This is a dermoscopic photograph of a skin lesion.
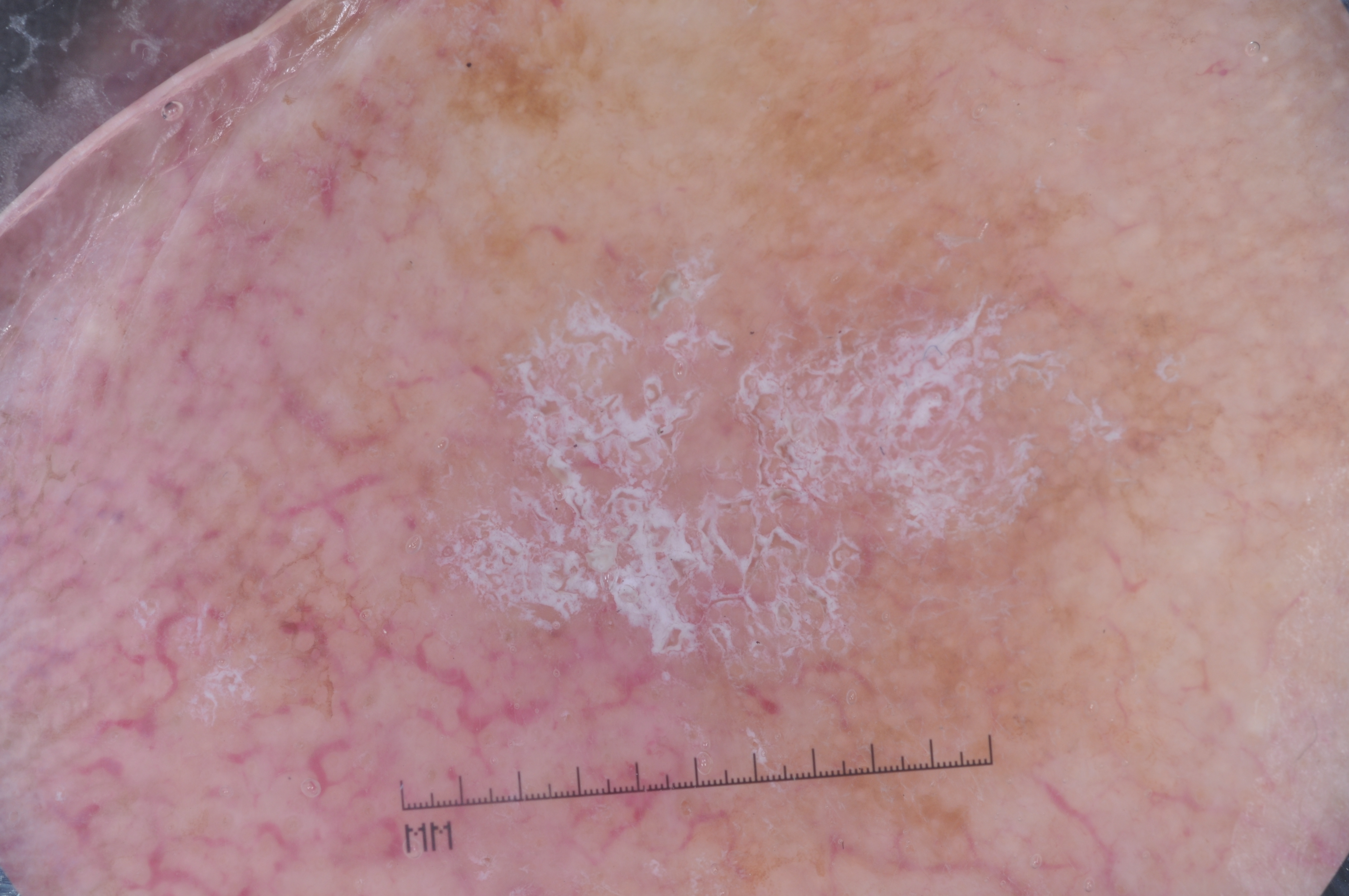Case summary: The lesion is clipped by the edge of the image. In (x1, y1, x2, y2) order, the lesion is bounded by bbox=[253, 0, 1222, 895]. A large lesion occupying much of the field. On dermoscopy, the lesion shows no negative network, pigment network, streaks, or milia-like cysts. Assessment: Consistent with a seborrheic keratosis.